A male subject in their mid-60s · Fitzpatrick skin type II · a clinical photograph of a skin lesion: 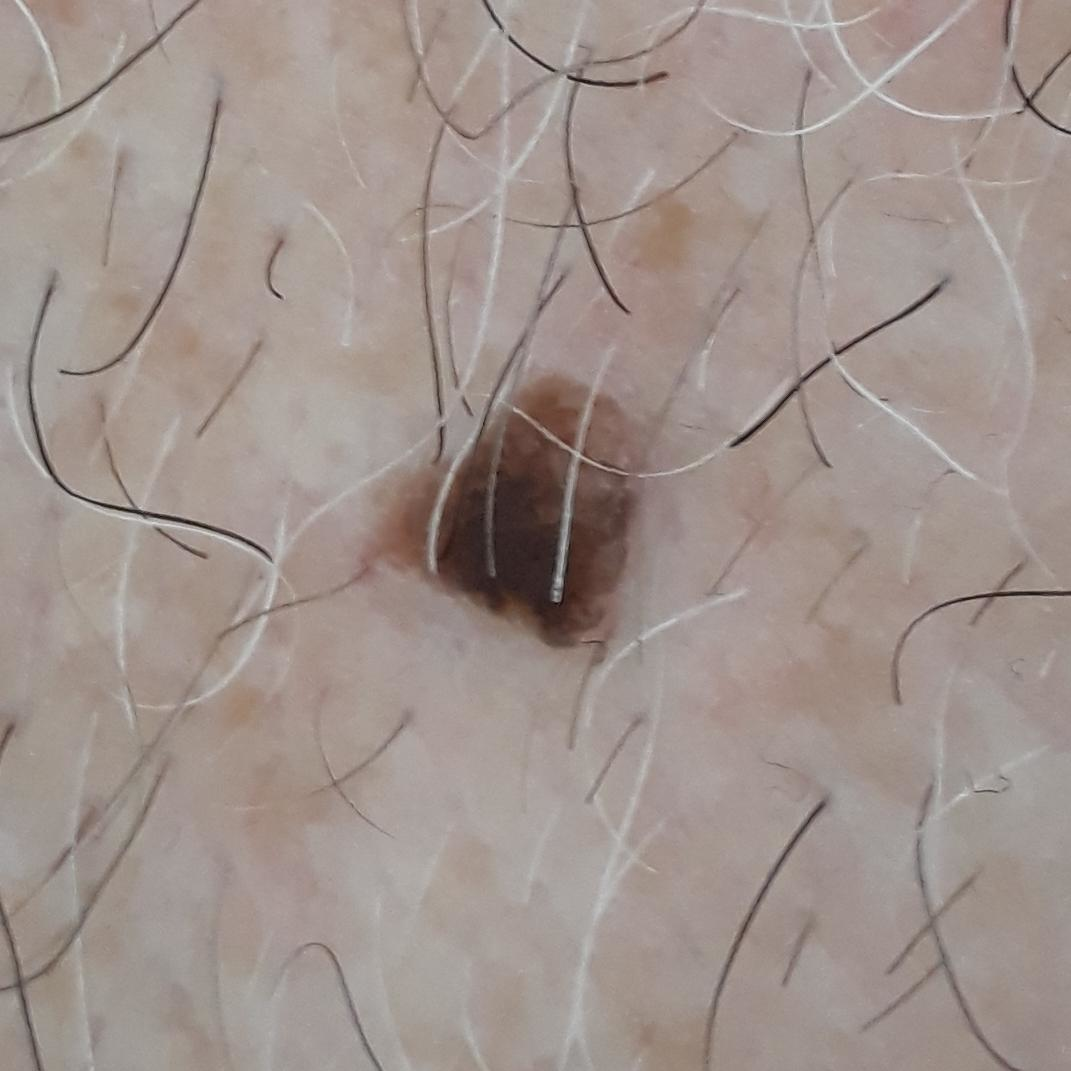Summary:
Measuring about 6 × 4 mm. By the patient's account, the lesion itches and is elevated.
Conclusion:
Expert review favored a benign lesion — a seborrheic keratosis.